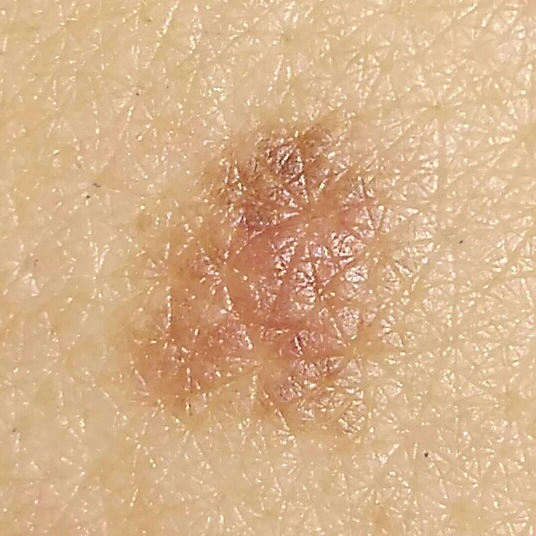diagnosis: nevus (biopsy-proven).